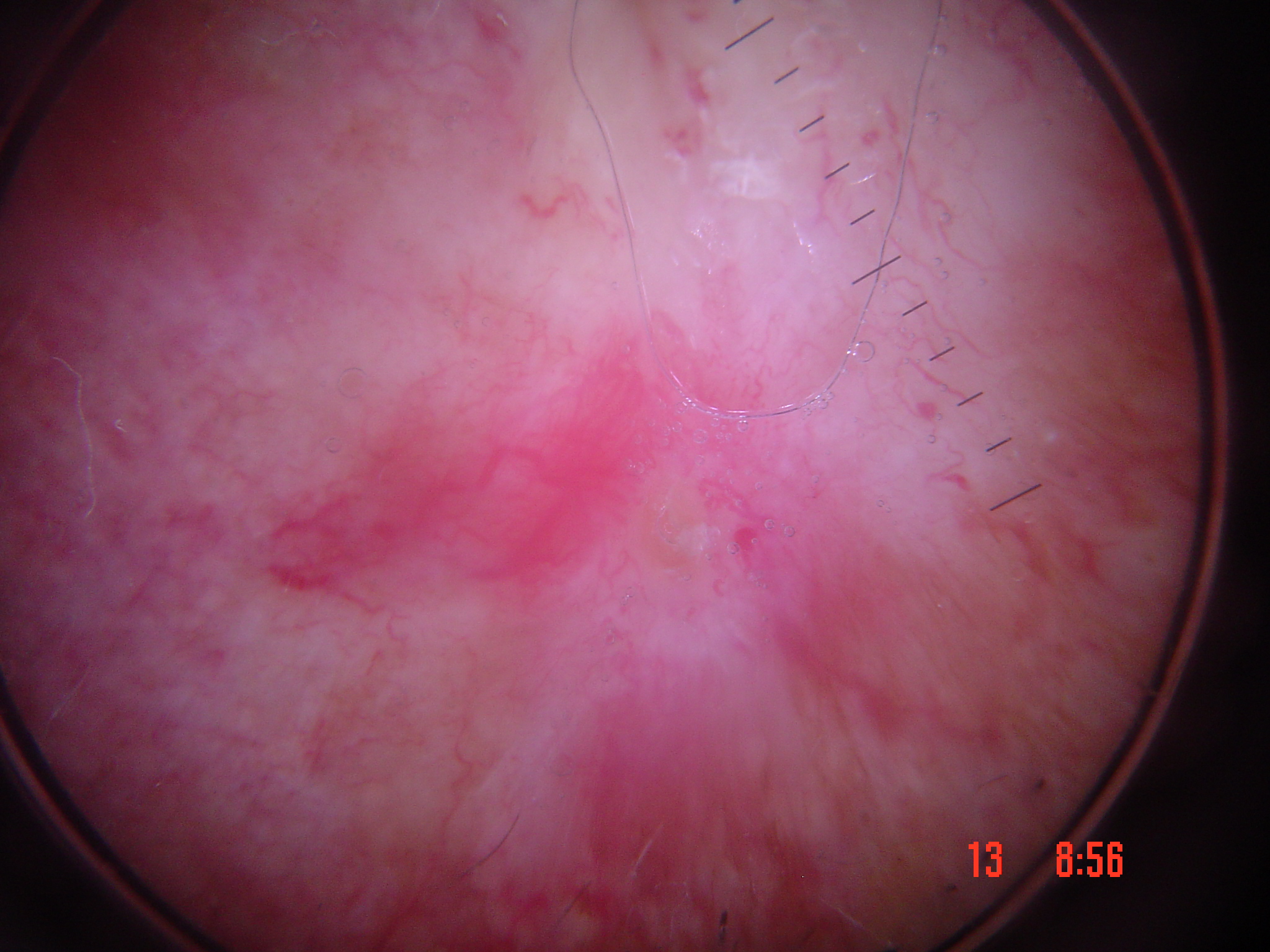Histopathologically confirmed as a basal cell carcinoma.